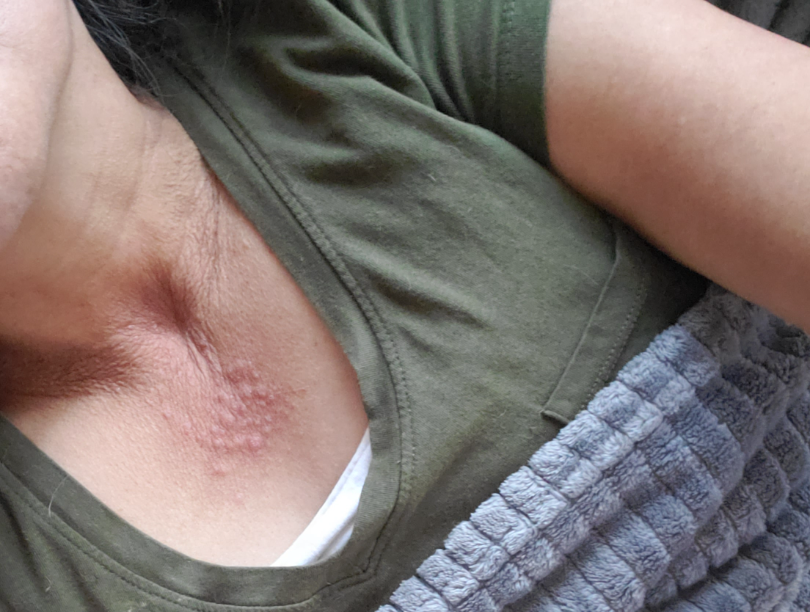Impression: The reviewing clinician's impression was: most consistent with Cutaneous lupus; also raised was Lichenified eczematous dermatitis; lower on the differential is Dermatomyositis.